A skin lesion imaged with a dermatoscope.
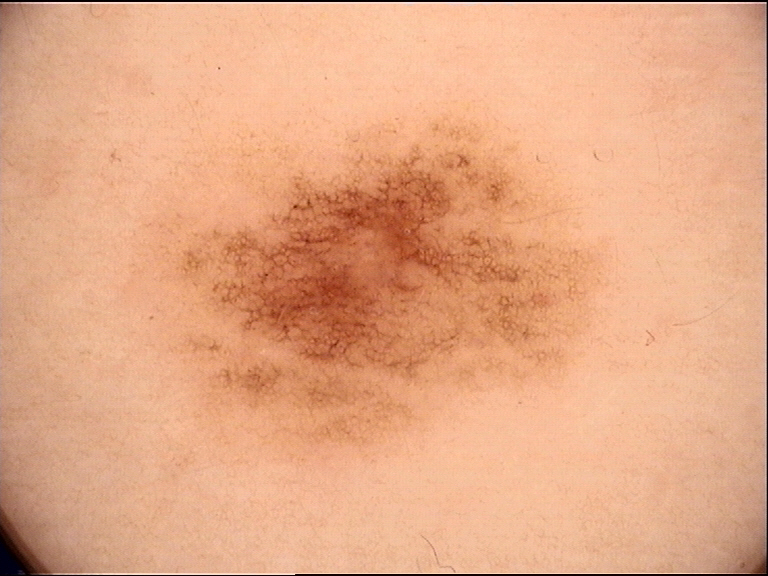label: dysplastic junctional nevus (expert consensus).